The front of the torso is involved · reported lesion symptoms include bothersome appearance and darkening · no constitutional symptoms were reported · the lesion is described as flat · the photo was captured at an angle · self-categorized by the patient as a rash · the subject is 18–29, male:
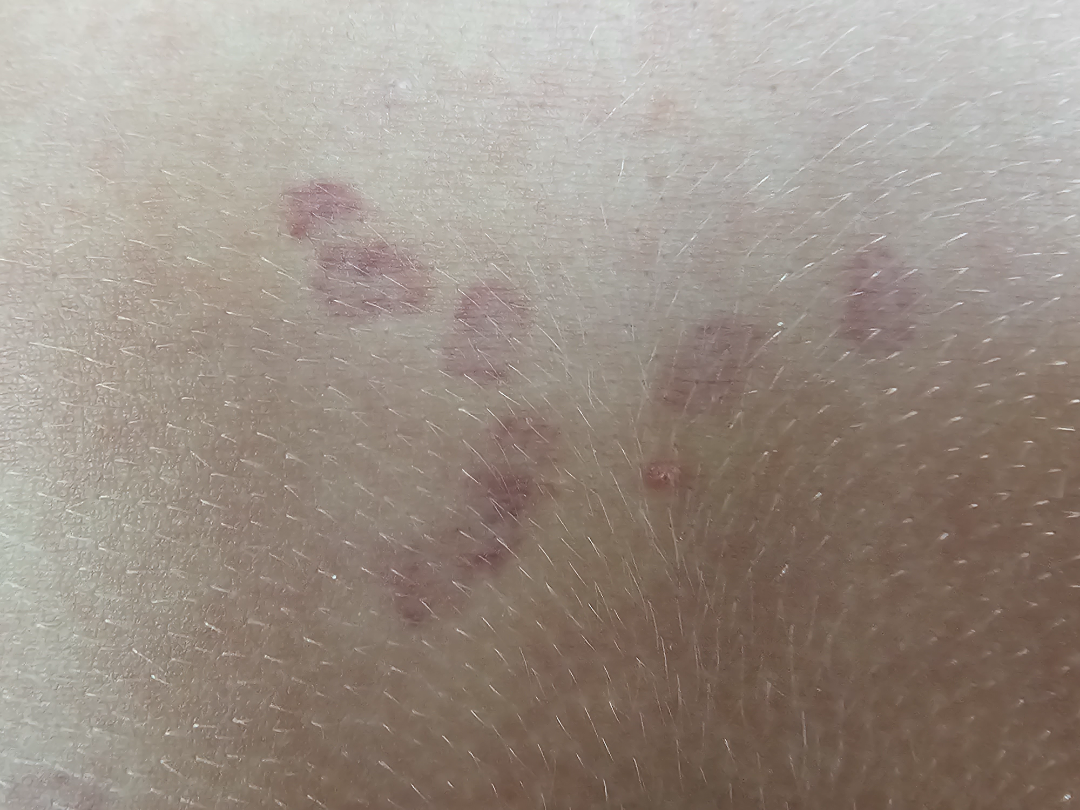The case was indeterminate on photographic review.